By history, no prior skin cancer (patient or family) and no tobacco use. A female patient 73 years old. A clinical close-up photograph of a skin lesion. The patient was assessed as skin type II — 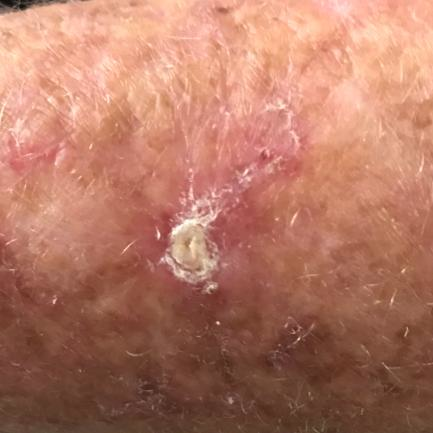Notes:
• site: a forearm
• lesion diameter: 9x6 mm
• symptoms: bleeding, itching, growth
• diagnostic label: actinic keratosis (clinical consensus)